A dermatoscopic image of a skin lesion.
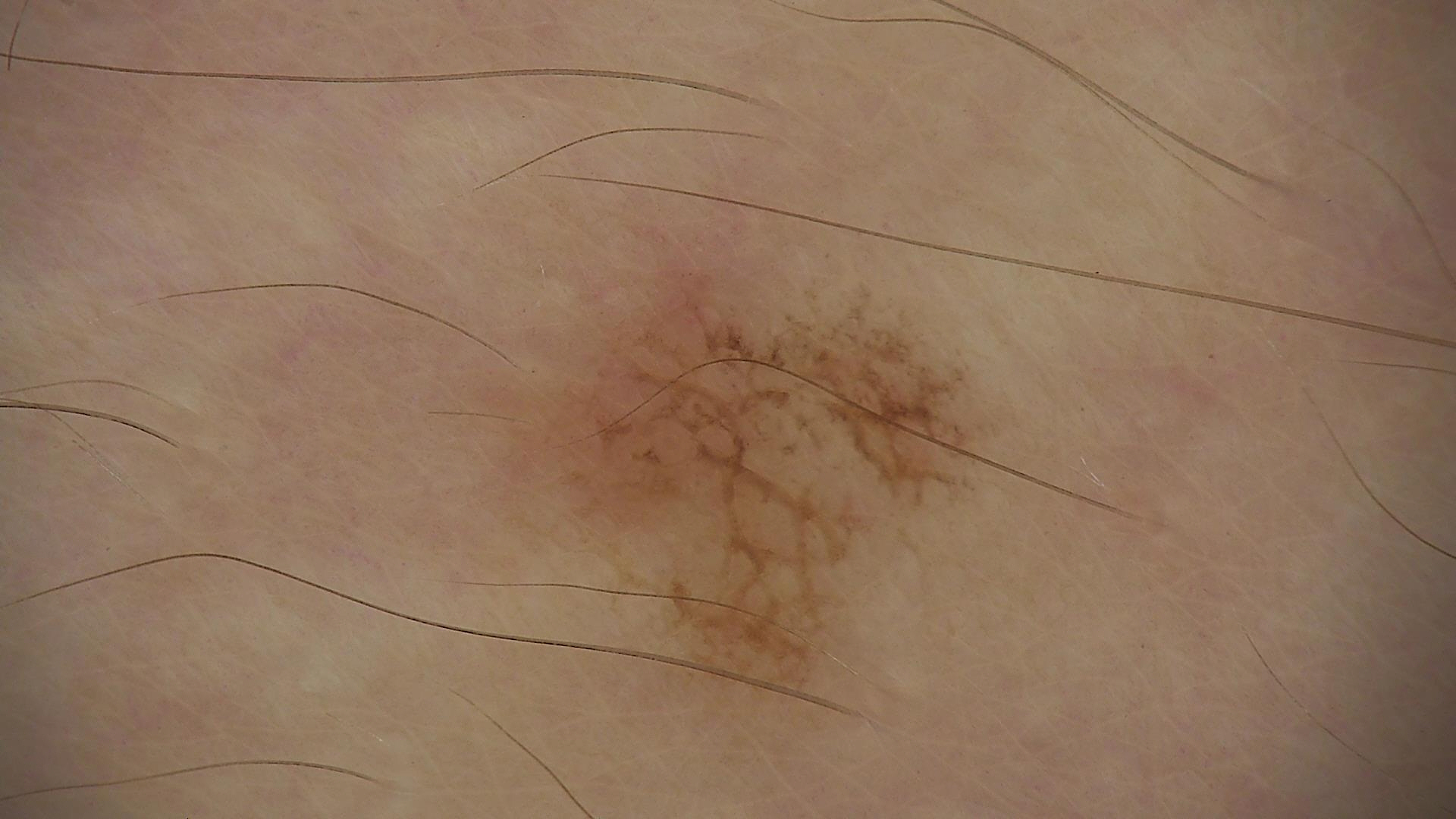Diagnosed as a dysplastic junctional nevus.